A dermatoscopic image of a skin lesion · a female patient, approximately 50 years of age — 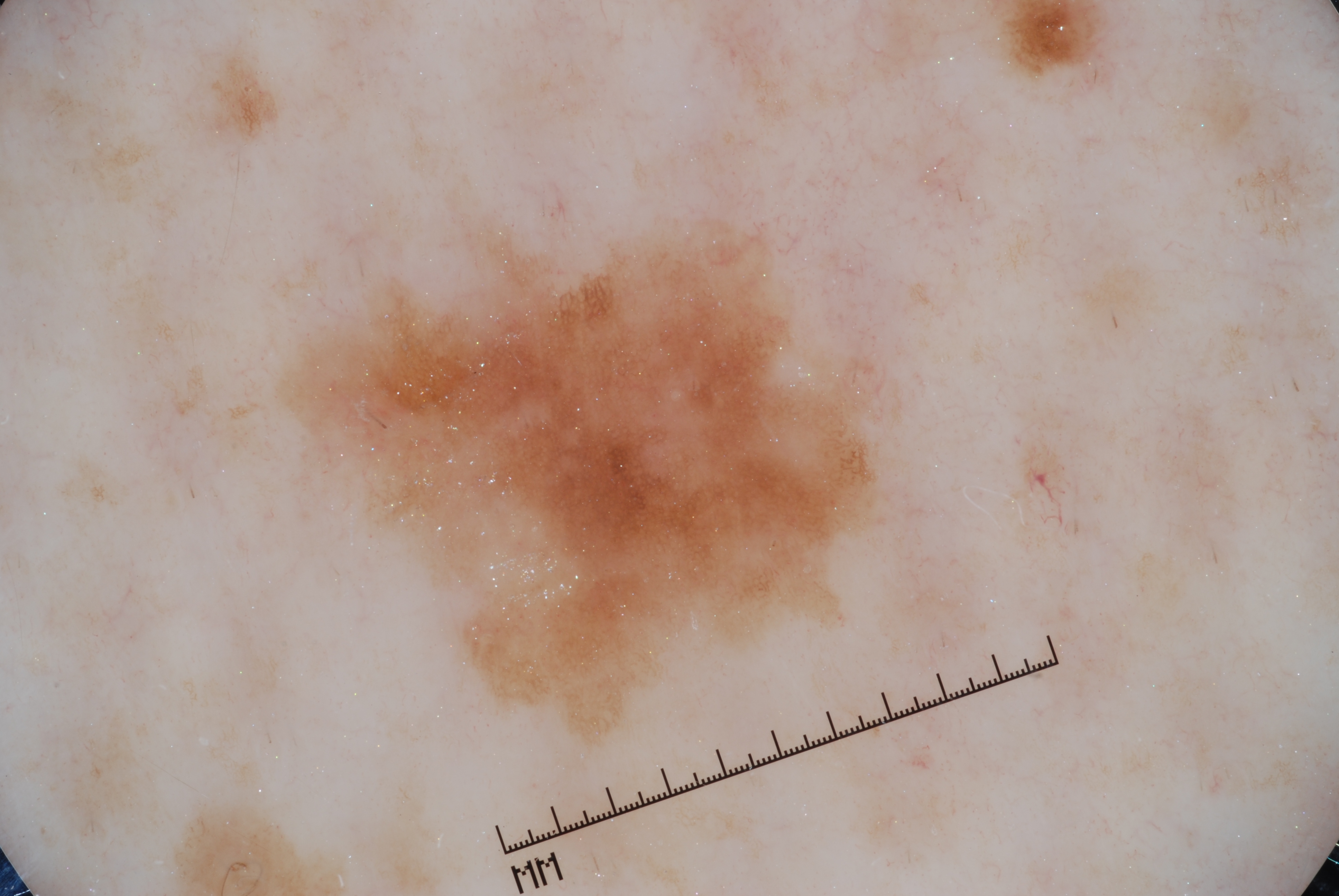bounding box: x1=293, y1=231, x2=878, y2=728; dermoscopic findings: pigment network; diagnosis: a seborrheic keratosis, a keratinocytic lesion.